A dermoscopy image of a single skin lesion.
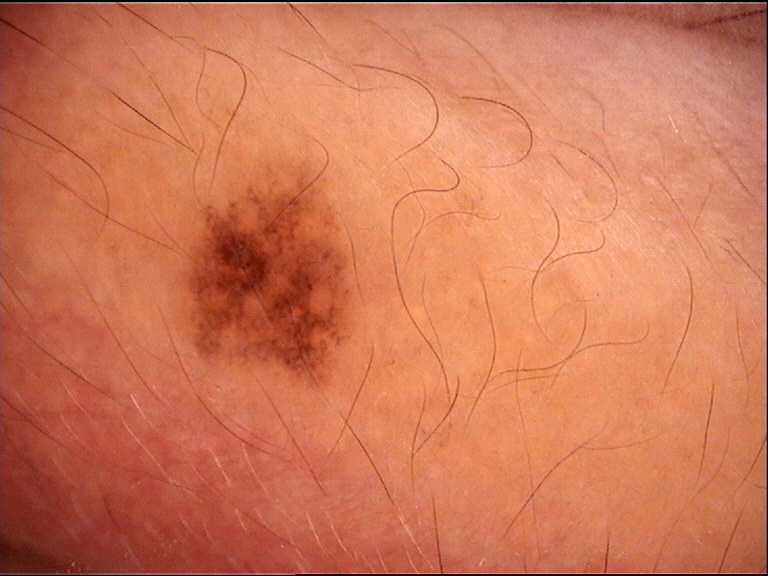diagnostic label=dysplastic junctional nevus (expert consensus)